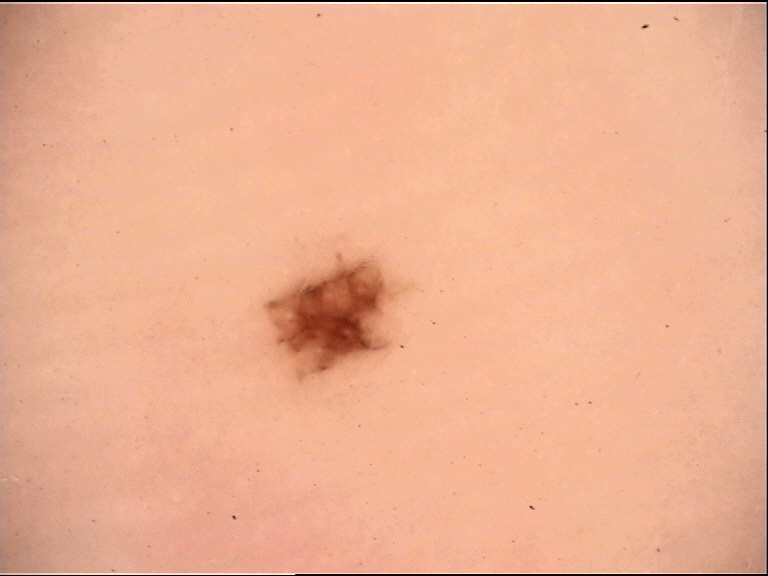Conclusion: Consistent with a benign lesion — an acral dysplastic junctional nevus.